The affected area is the back of the hand; male subject, age 50–59; an image taken at a distance.
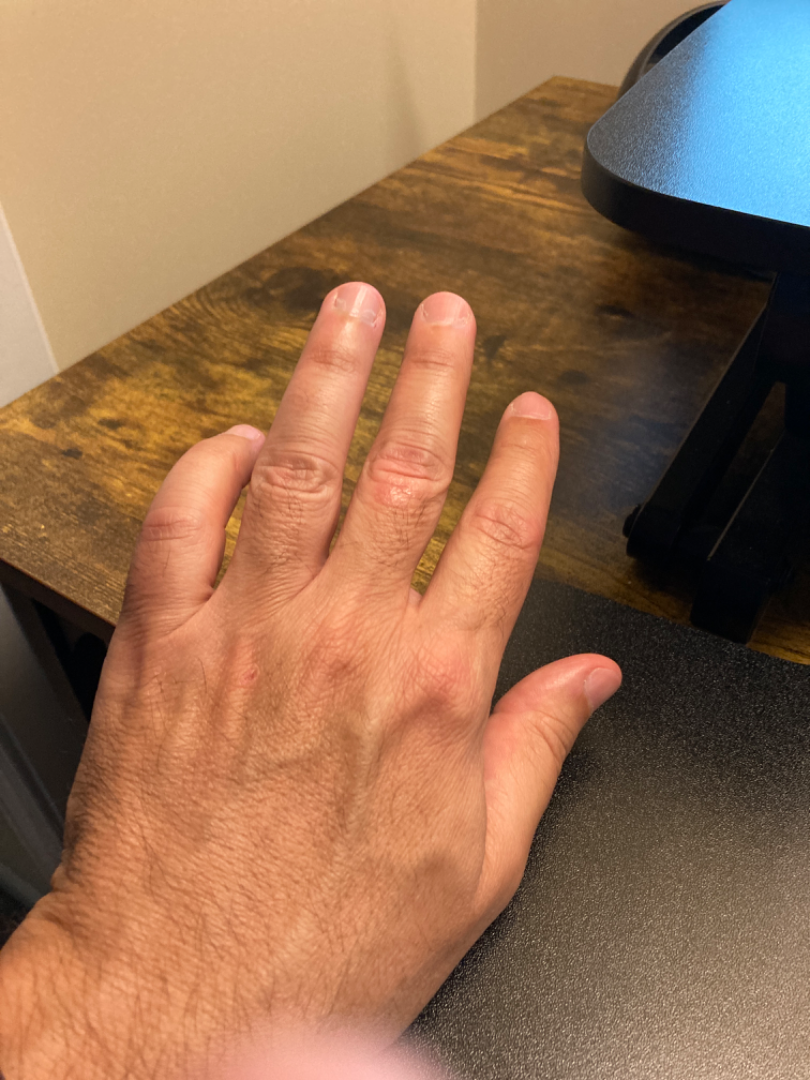The image was not sufficient for the reviewer to characterize the skin condition.